The lesion involves the leg · this image was taken at a distance.
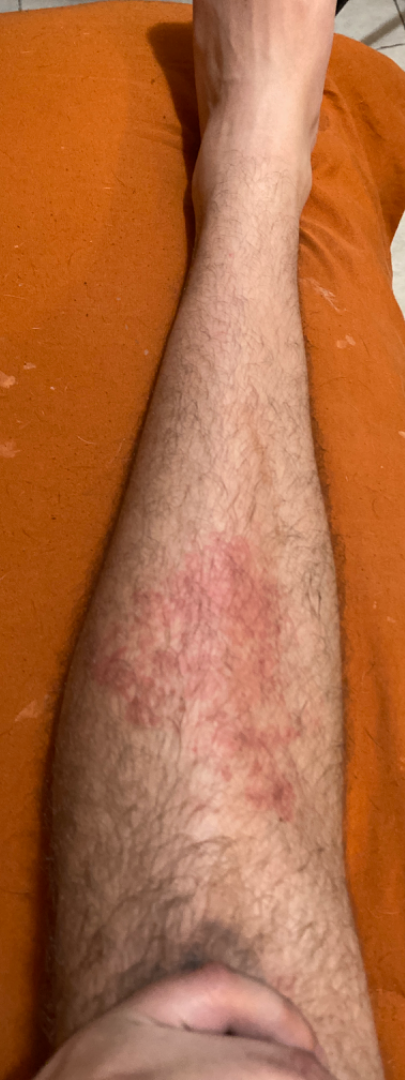* assessment · unable to determine